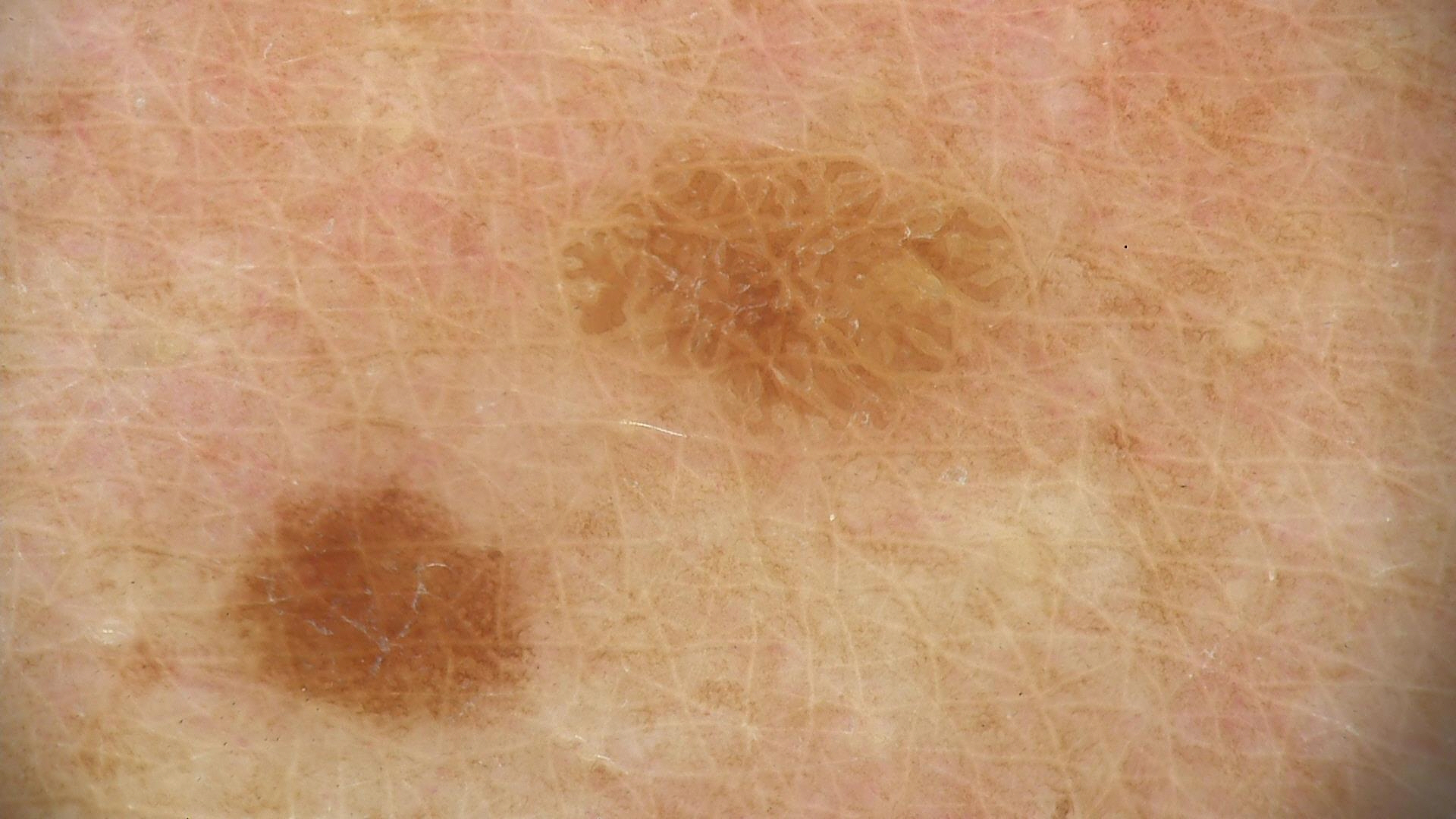label: seborrheic keratosis (expert consensus).